A moderate number of moles by the patient's own estimate. By self-report, no immunosuppression. A skin lesion imaged with a dermatoscope. Acquired for a research image collection, with no referral diagnosis. A male subject aged 72. The patient says their skin tans without first burning: 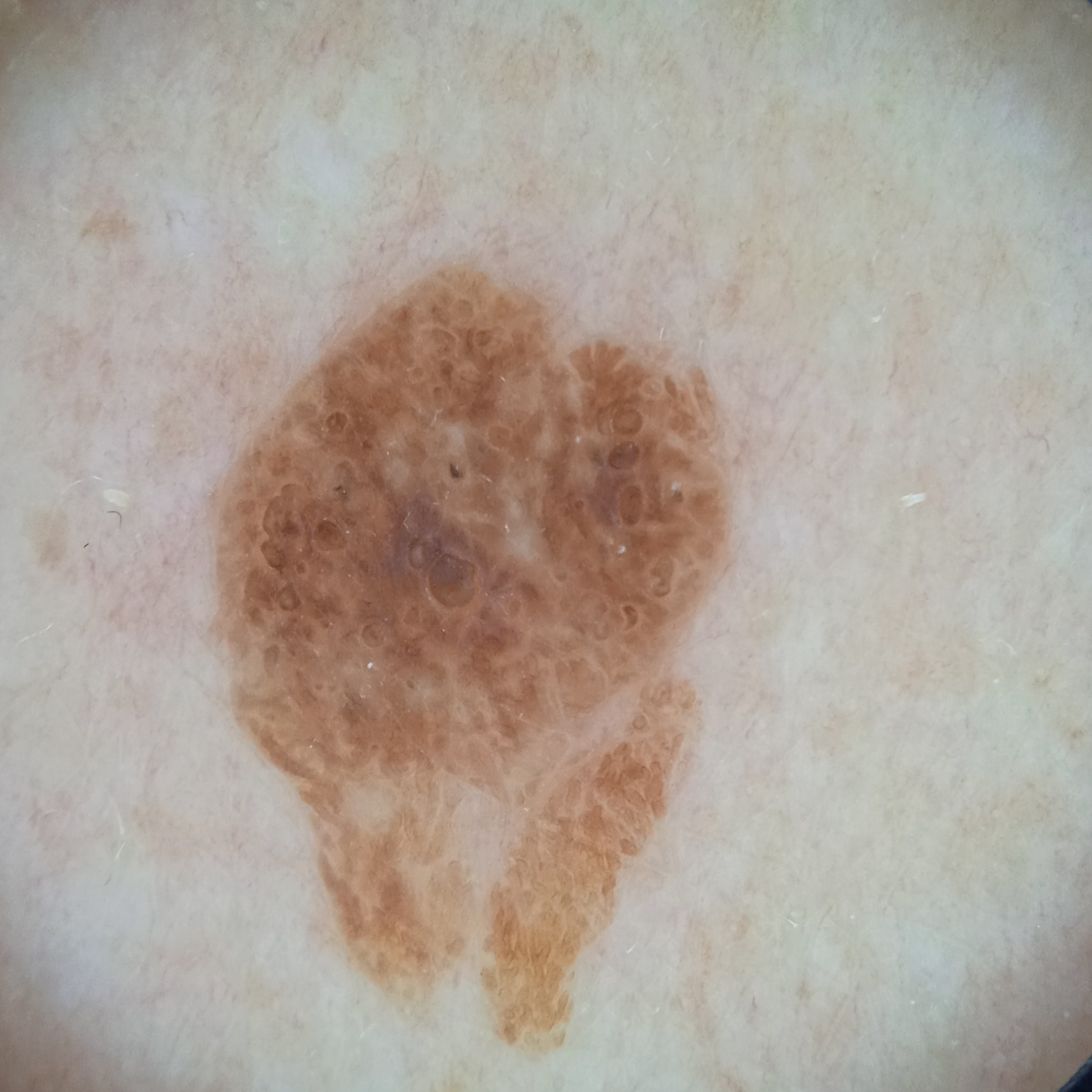body site = the back, size = 9.6 mm, diagnosis = seborrheic keratosis (dermatologist consensus).